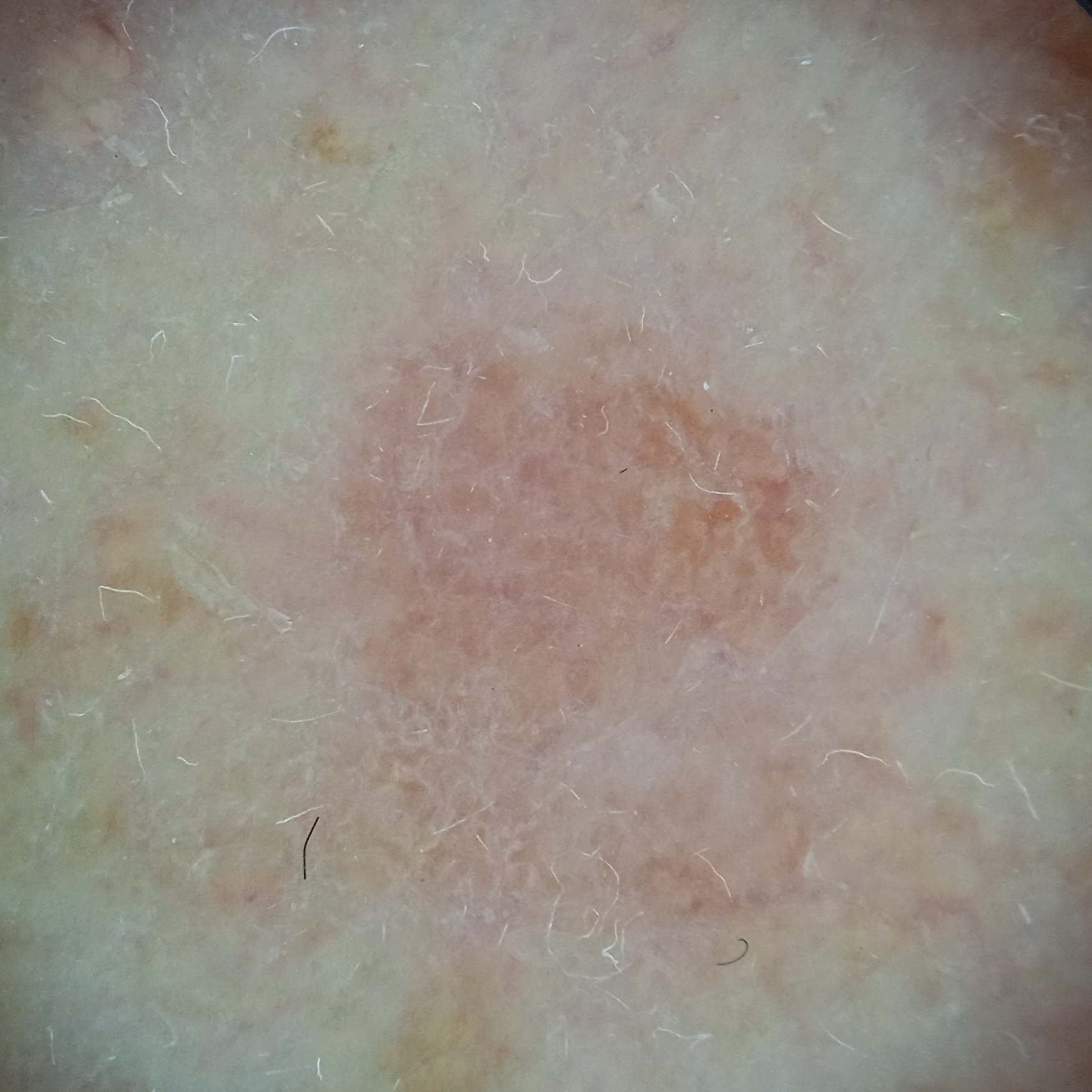Case summary:
Referred for assessment of suspected basal cell carcinoma. A female subject 55 years of age. Dermoscopy of a skin lesion. The lesion is on the face. The lesion measures approximately 5.7 mm.
Impression:
On independent review by four dermatologists, the agreed diagnosis was an actinic keratosis; all four reviewers agreed; the reviewers were moderately confident.